Dermoscopy of a skin lesion, a female patient aged approximately 35: 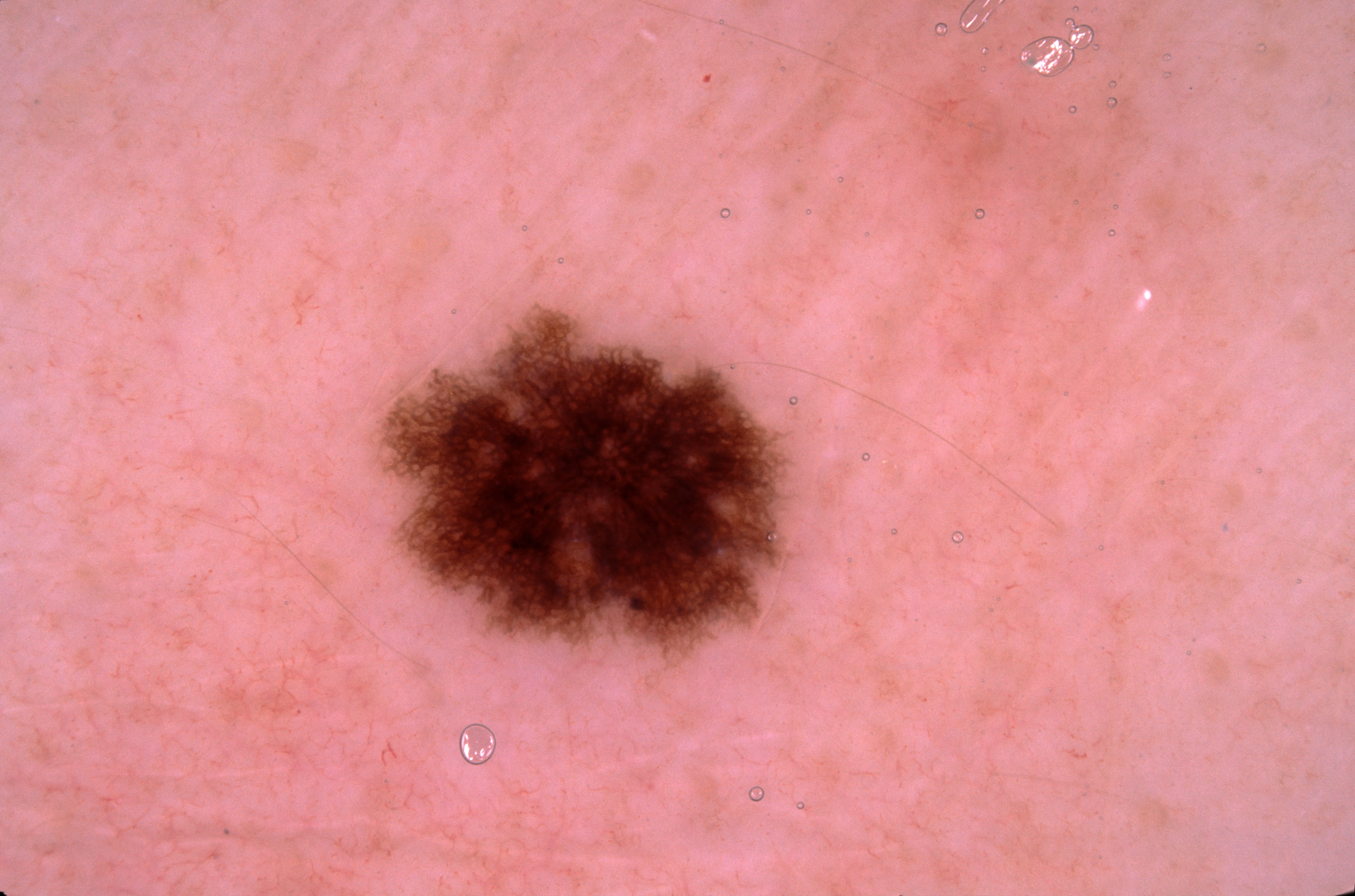The lesion is bounded by x1=392, y1=322, x2=783, y2=644. Dermoscopy demonstrates pigment network, with no streaks, negative network, or milia-like cysts. Clinically diagnosed as a melanocytic nevus.